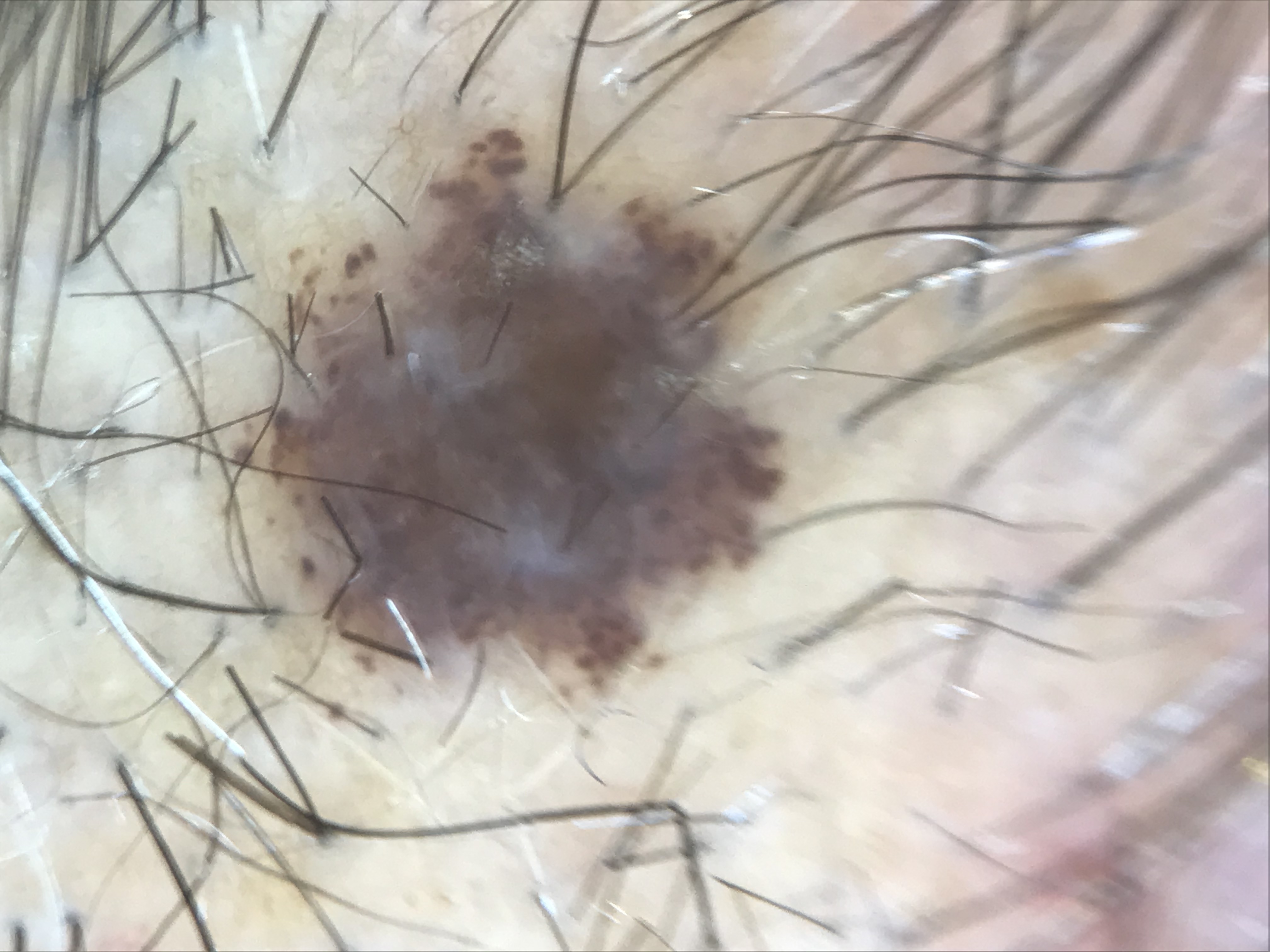A skin lesion imaged with a dermatoscope. Consistent with a dysplastic compound nevus.